A skin lesion imaged with a dermatoscope:
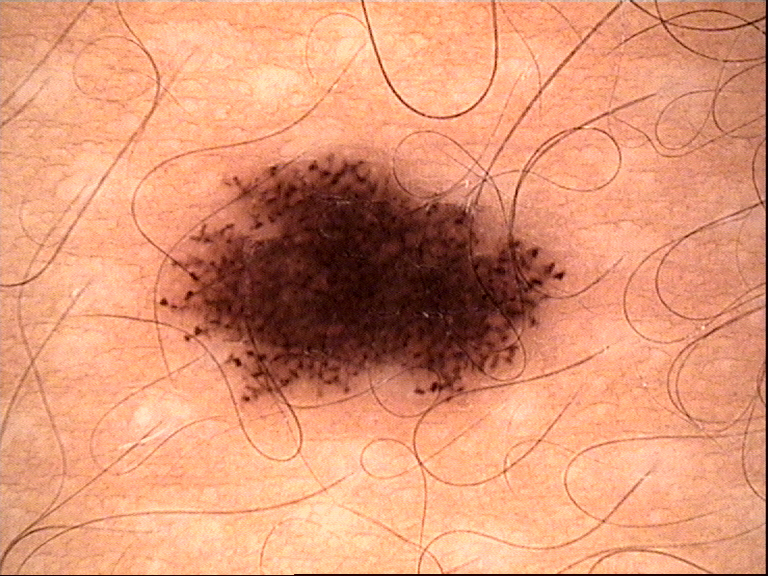Labeled as a benign lesion — a dysplastic junctional nevus.